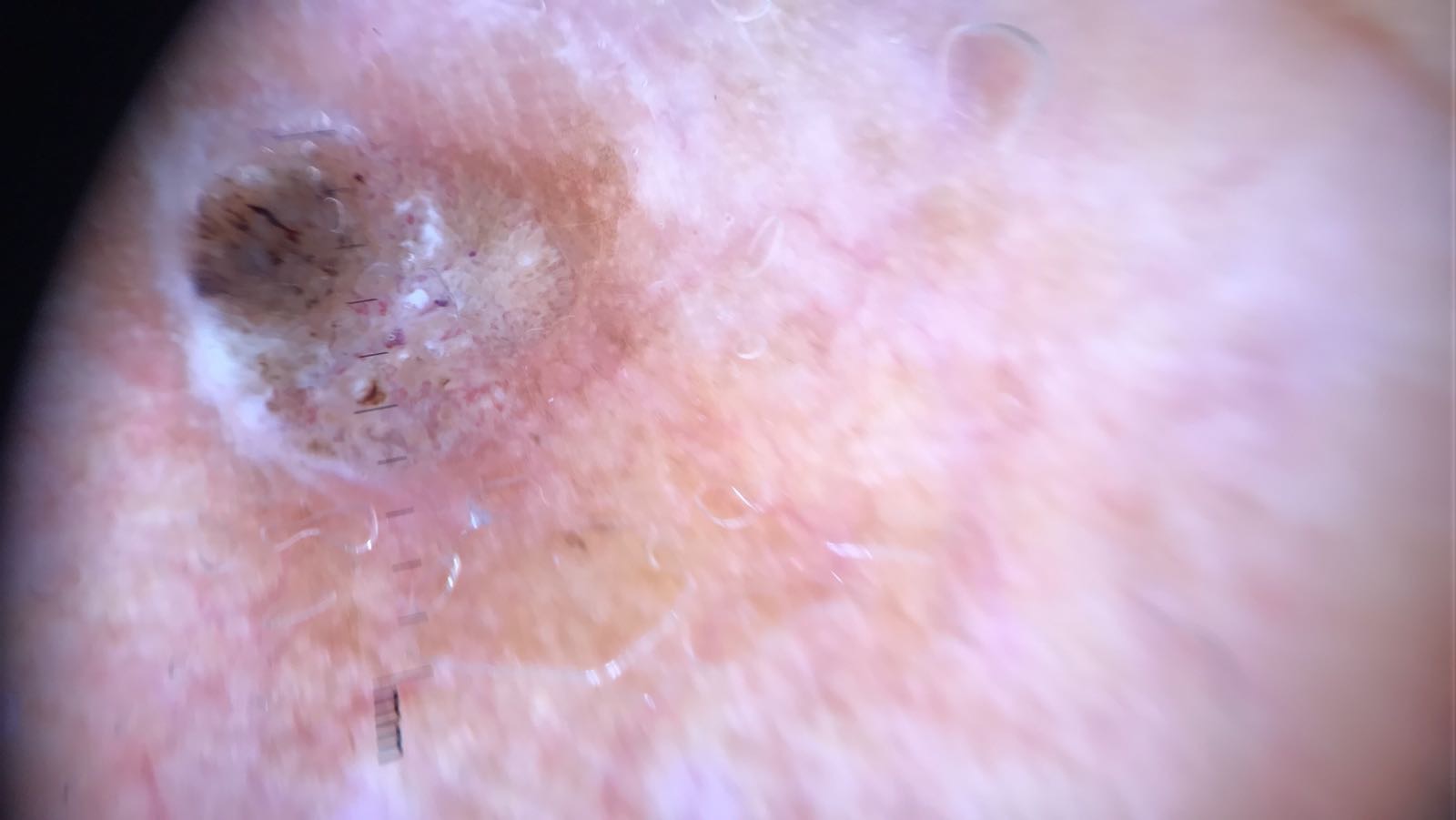Conclusion: Labeled as a seborrheic keratosis.